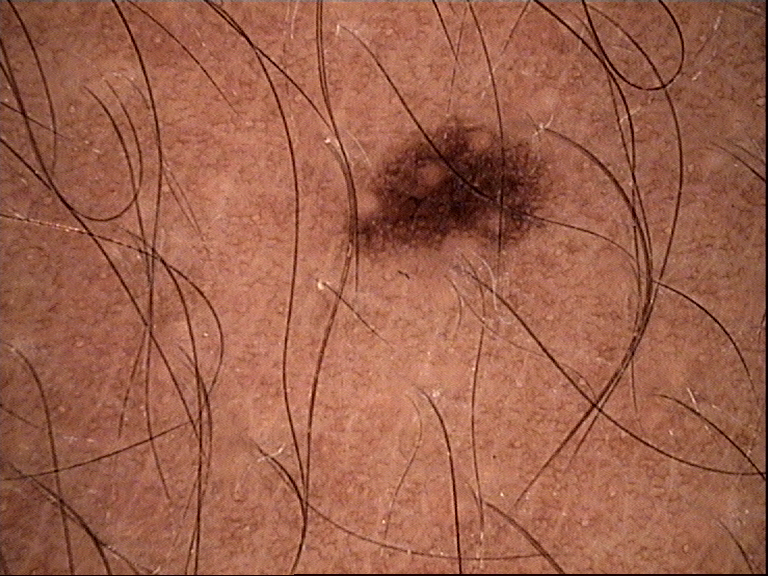Consistent with a dysplastic junctional nevus.